The affected area is the back of the torso and front of the torso; the photo was captured at a distance — 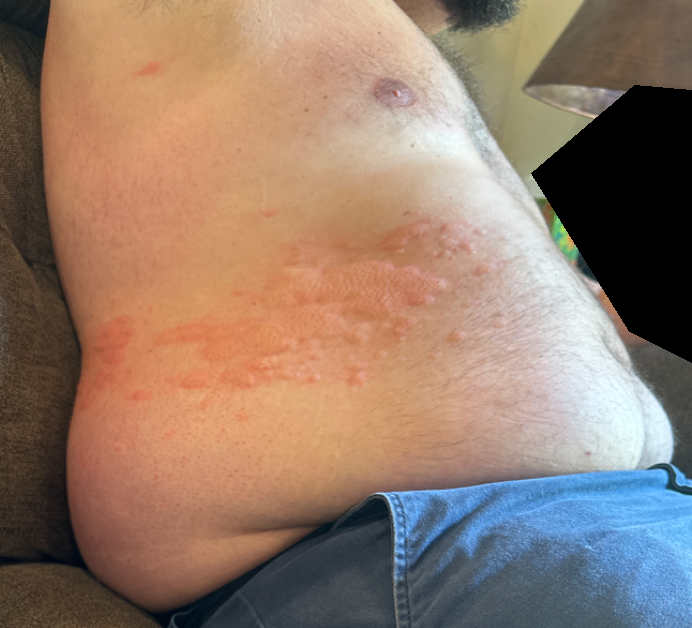Findings: Single-reviewer assessment: the reviewer's impression was Urticaria.